A skin lesion imaged with a dermatoscope.
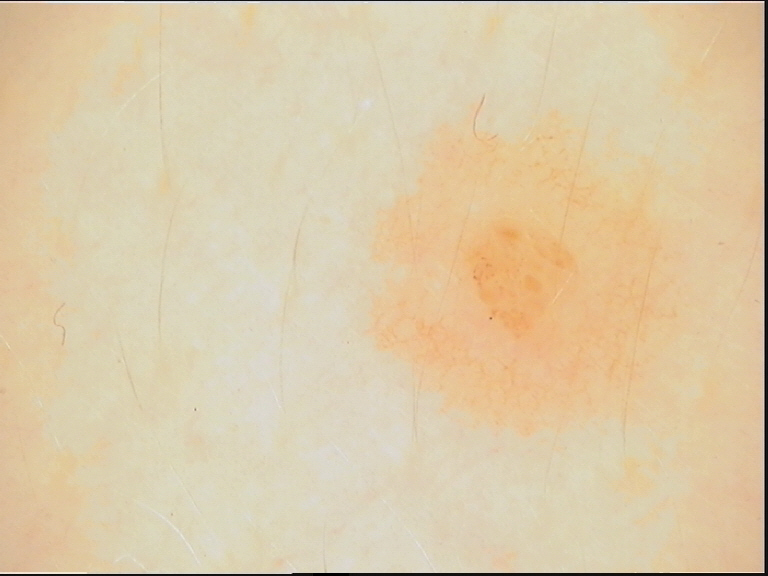diagnostic label: dysplastic junctional nevus (expert consensus).